A skin lesion imaged with a dermatoscope · a male patient age 89:
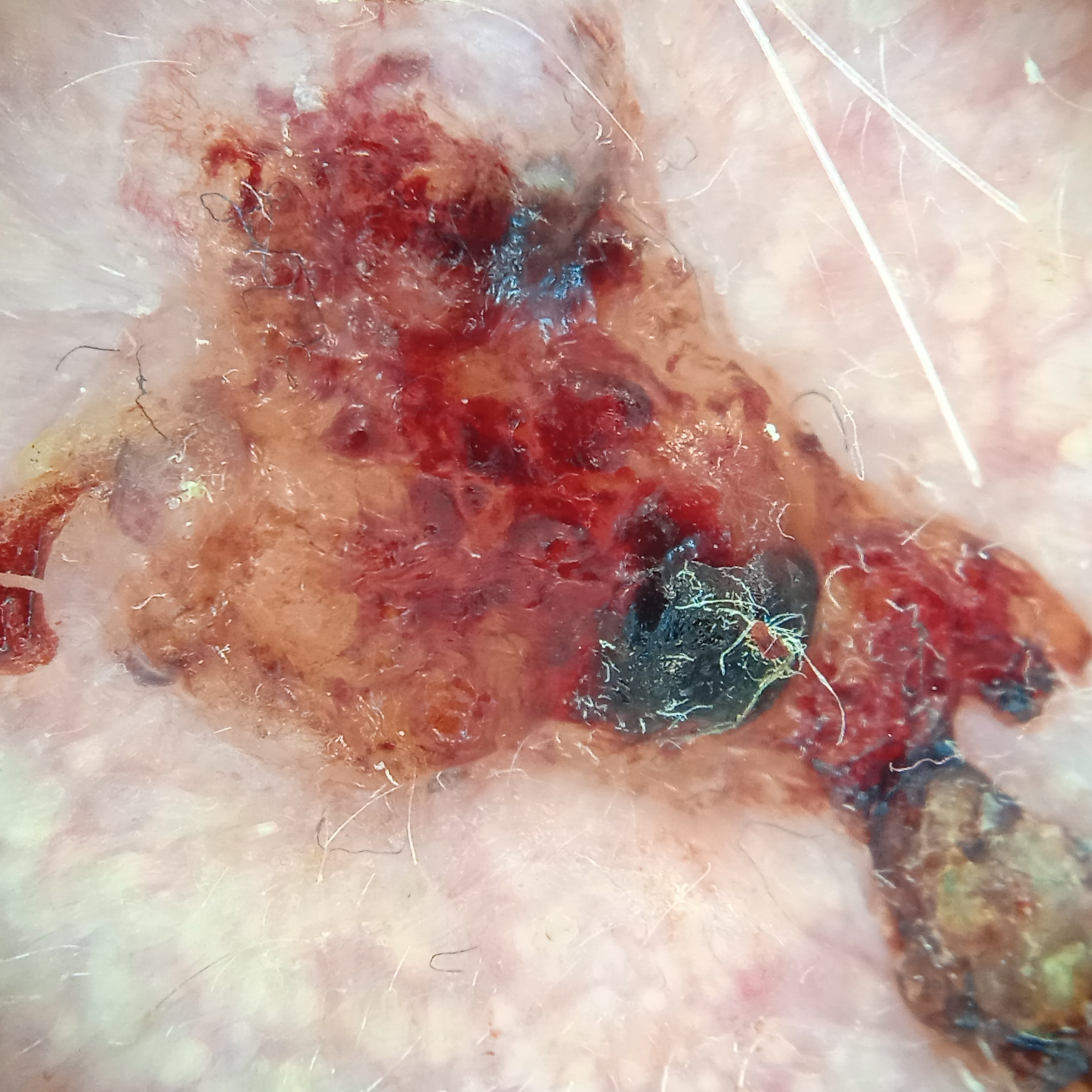site = the face
diagnostic label = basal cell carcinoma (biopsy-proven)